Symptoms reported: burning and itching; close-up view — 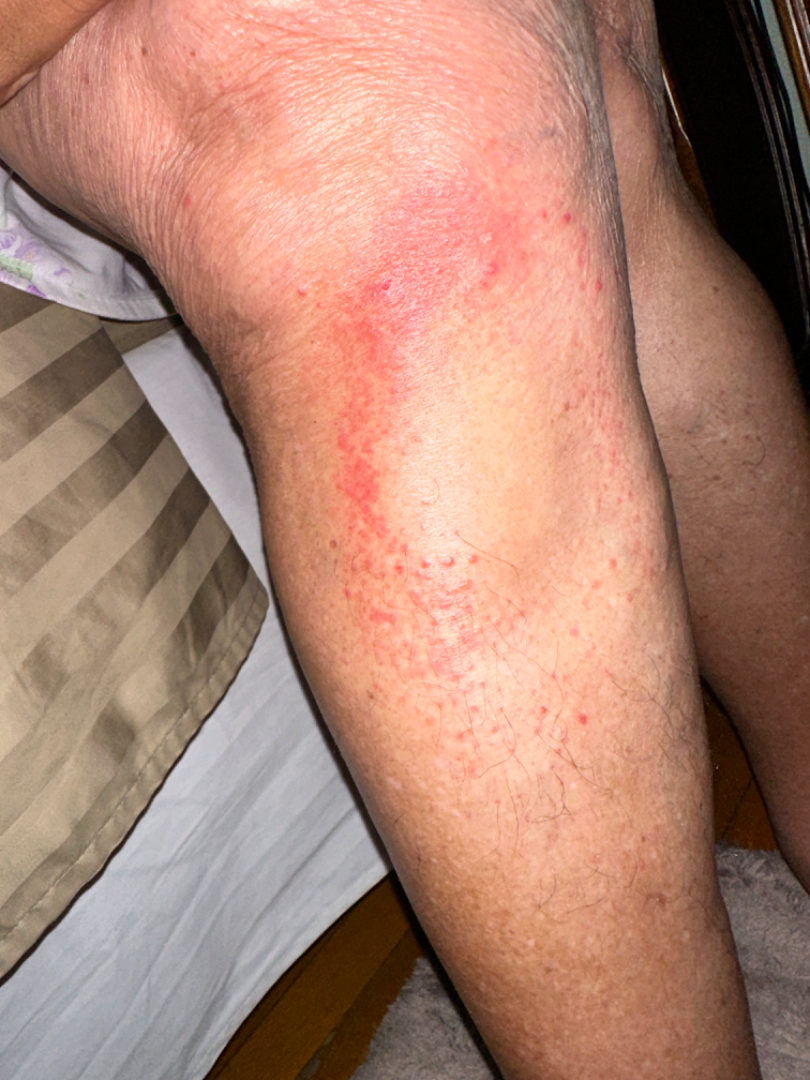{
  "assessment": "ungradable on photographic review"
}